The condition has been present for one to three months. The contributor is 60–69, female. The lesion is associated with burning, itching, darkening and enlargement. An image taken at an angle. The patient reported no systemic symptoms. The affected area is the arm, leg and back of the torso: 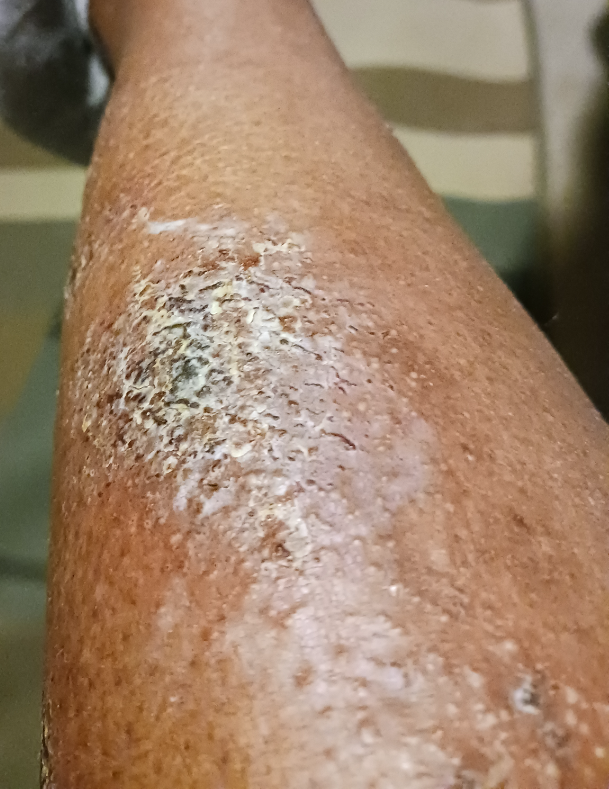Assessment: Eczema (0.52); Stasis Dermatitis (0.39); Psoriasis (0.09).